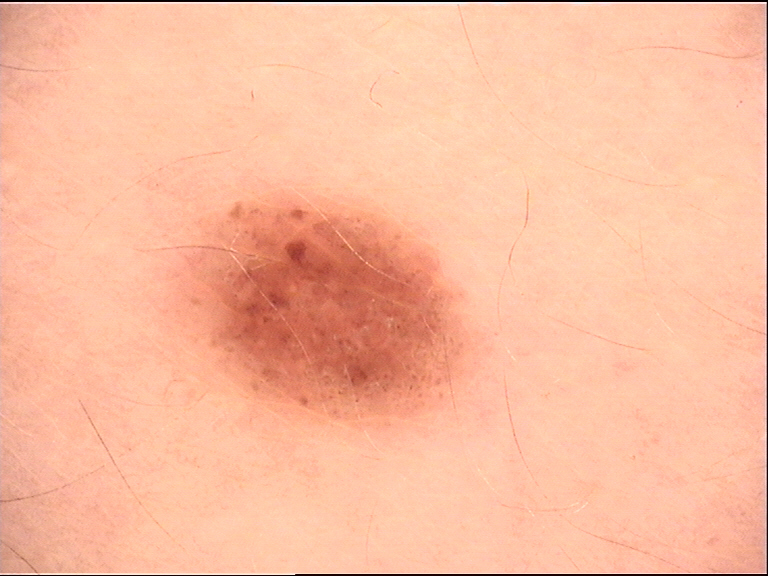Q: What kind of image is this?
A: dermatoscopy
Q: What was the diagnostic impression?
A: dysplastic junctional nevus (expert consensus)